The arm is involved · the photograph was taken at an angle · the subject is 40–49, female: 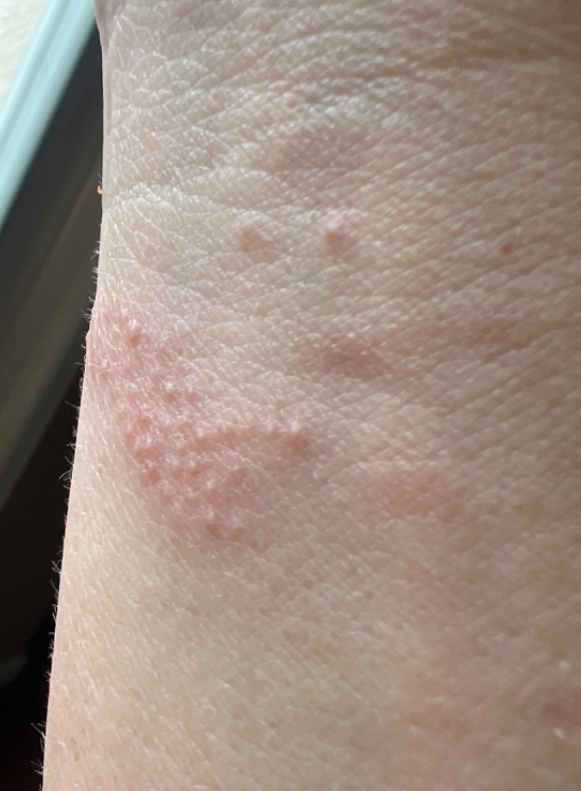Assessment: On photographic review: favoring Allergic Contact Dermatitis; with consideration of Herpes Simplex; also raised was Eczema; less probable is Lichen nitidus.